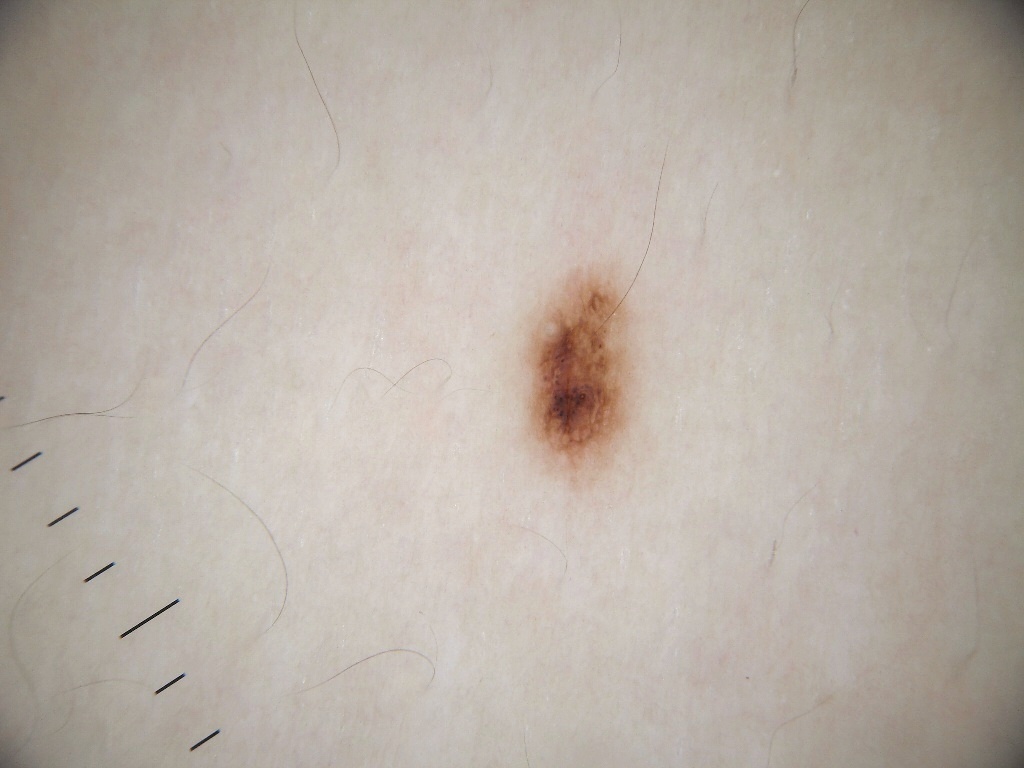subject — female, aged around 15
imaging — dermoscopy of a skin lesion
lesion size — ~2% of the field
lesion bbox — bbox=[522, 268, 635, 478]
features — pigment network; absent: negative network, streaks, milia-like cysts, and globules
impression — a melanocytic nevus